The photograph was taken at an angle: 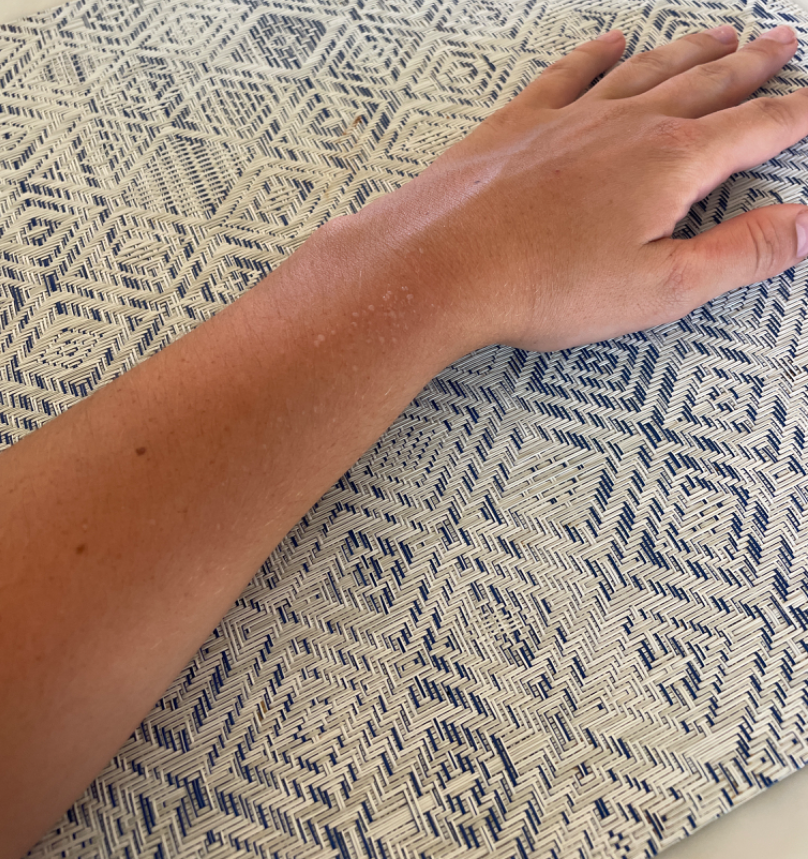assessment = indeterminate.